The photograph was taken at a distance:
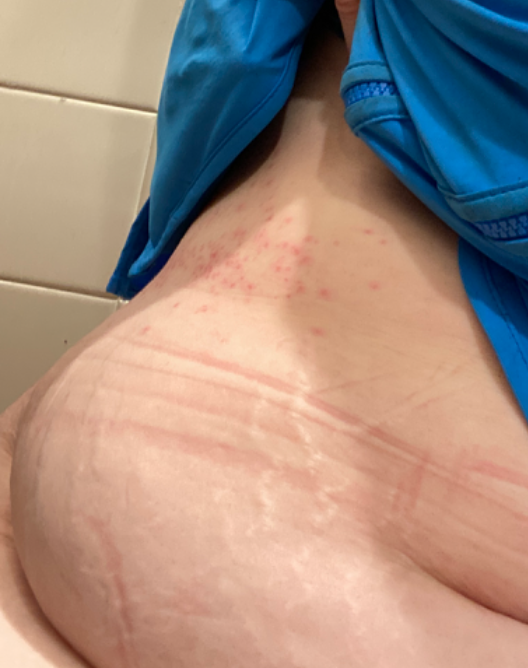assessment = reviewed remotely by one dermatologist: the impression was split between Intertrigo and Herpes Zoster; less likely is Irritant Contact Dermatitis